Reported duration is one to four weeks, the affected area is the leg, the photograph is a close-up of the affected area, texture is reported as raised or bumpy, FST III; lay reviewers estimated Monk Skin Tone 1 or 2 (two reviewer pools): 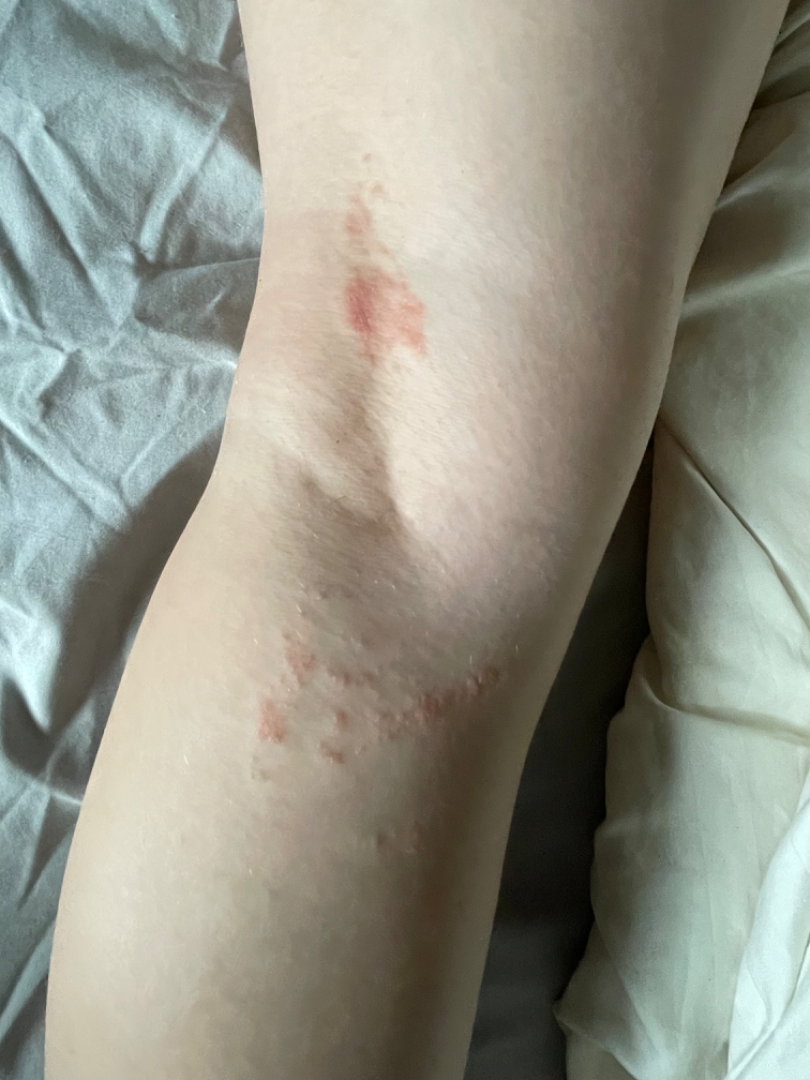Findings: Diagnostic features were not clearly distinguishable in this photograph.